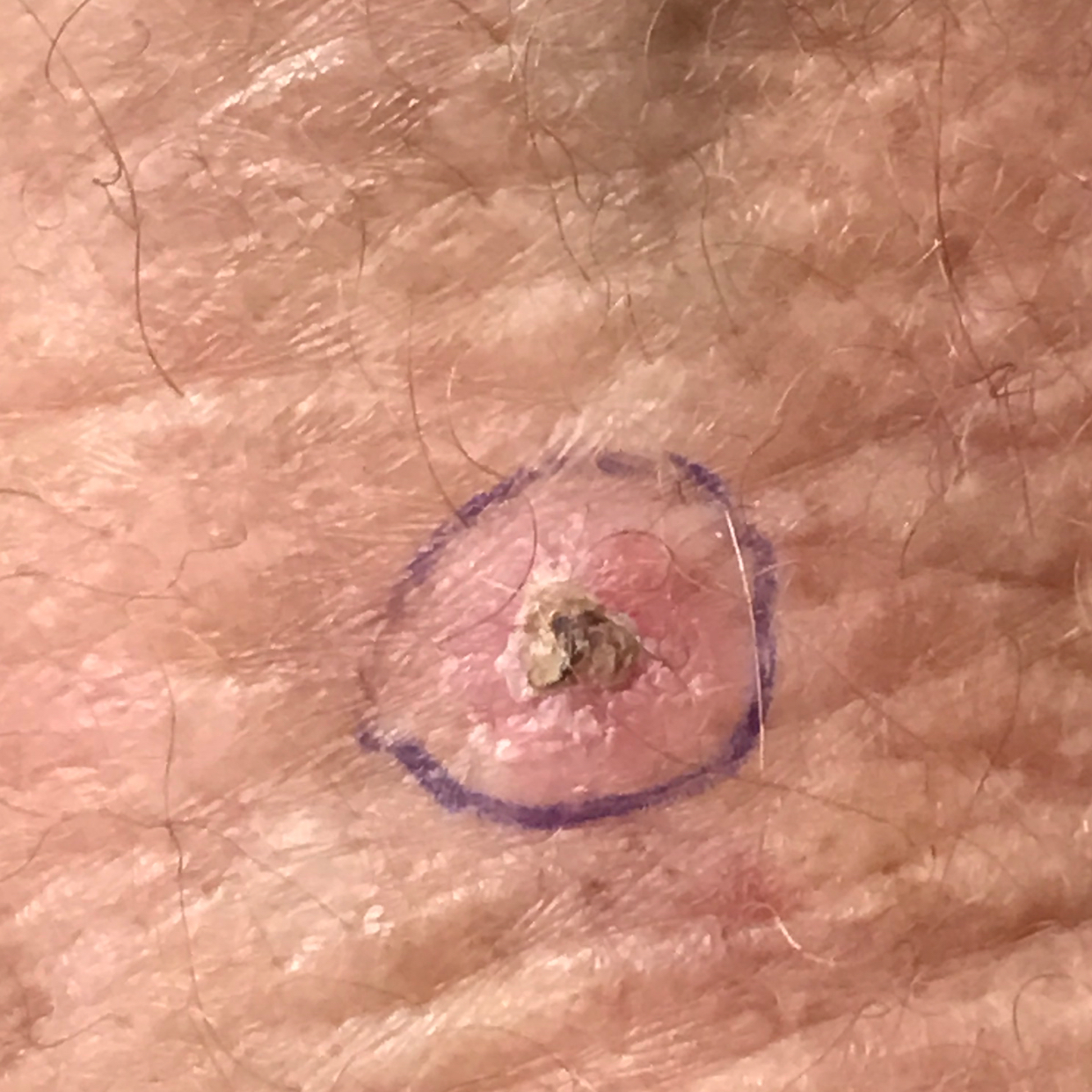Summary: A smartphone photograph of a skin lesion. Located on a forearm. The patient describes that the lesion itches and is elevated. Conclusion: The consensus clinical diagnosis was an actinic keratosis.